This image was taken at a distance. The lesion involves the leg. The patient is 30–39, female: 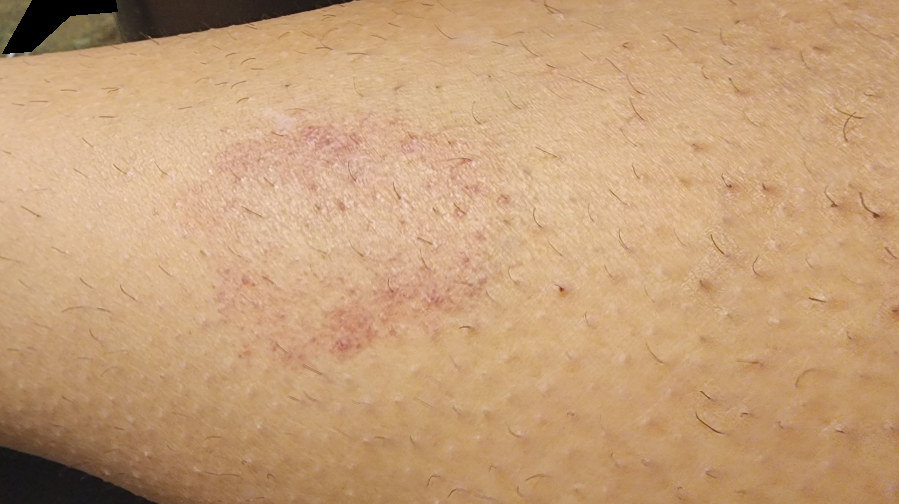  differential:
    leading:
      - Purpura
    considered:
      - Hemangioma
      - Drug Rash